The patient is a female aged 30–39. The back of the hand, arm and back of the torso are involved. Texture is reported as raised or bumpy. Reported duration is about one day. This is a close-up image. Skin tone: Fitzpatrick IV. The patient described the issue as a rash:
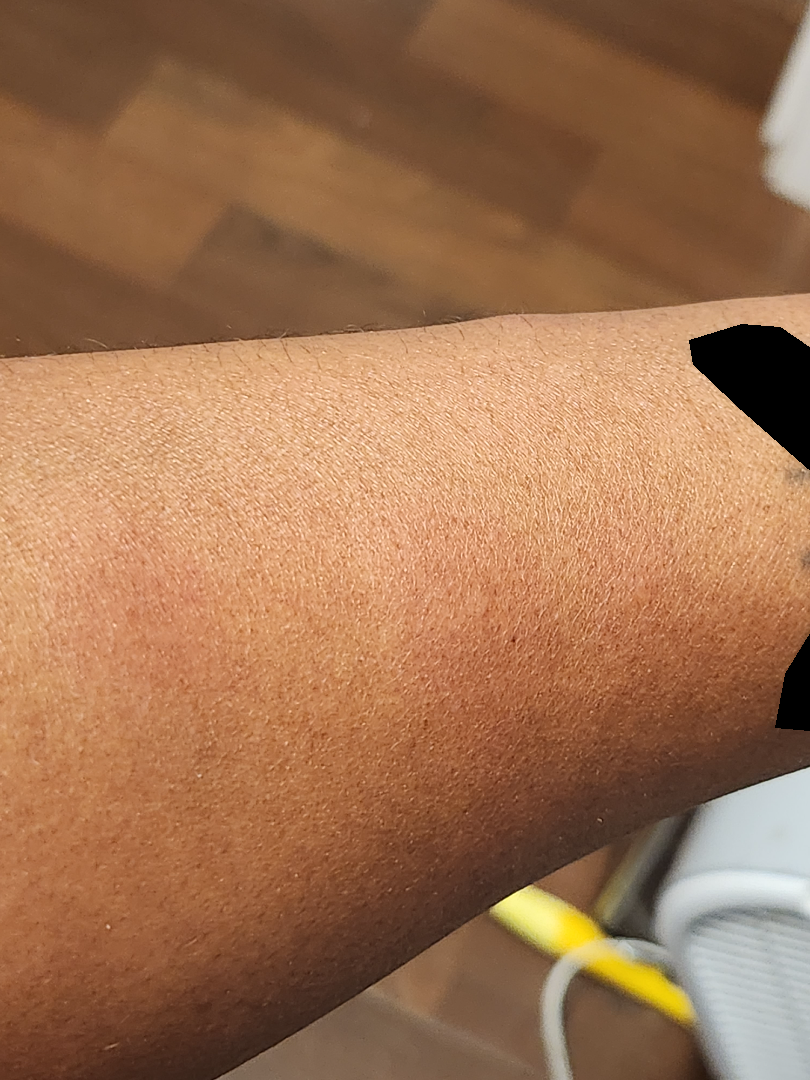Most likely Cutaneous lupus; also consider Urticaria.